A female subject in their 60s:
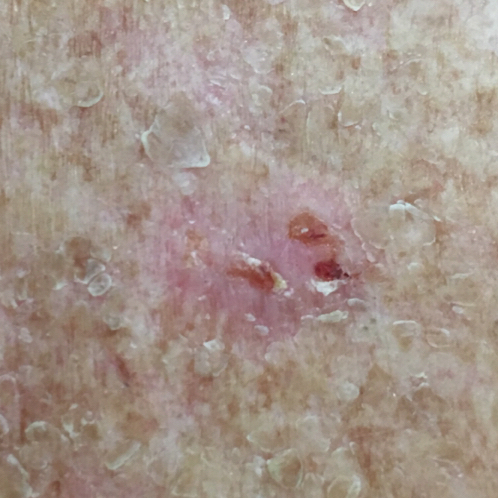<skin_lesion>
  <lesion_location>the back</lesion_location>
  <symptoms>
    <present>bleeding, itching, growth, elevation, change in appearance</present>
  </symptoms>
  <diagnosis>
    <name>squamous cell carcinoma</name>
    <code>SCC</code>
    <malignancy>malignant</malignancy>
    <confirmation>histopathology</confirmation>
  </diagnosis>
</skin_lesion>